A subject in their 40s:
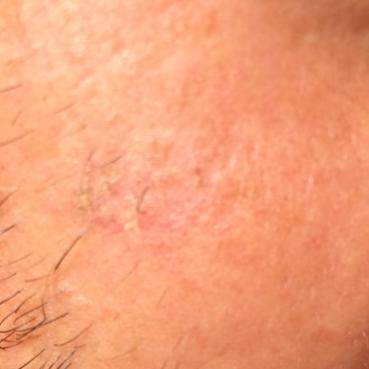The lesion was found on the face. The clinical impression was an actinic keratosis.